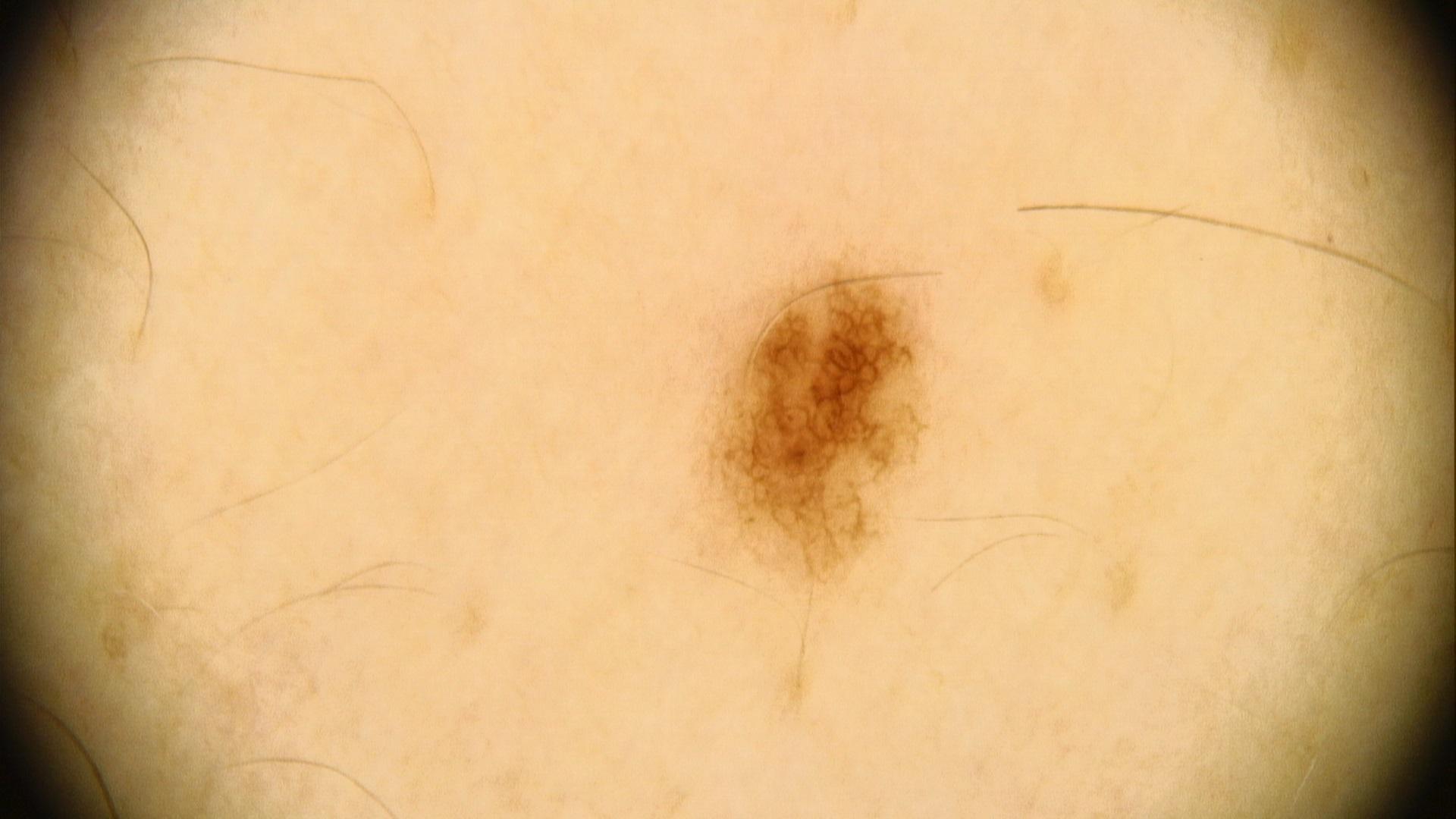Q: What is the diagnosis?
A: Nevus (clinical impression)